Close-up view:
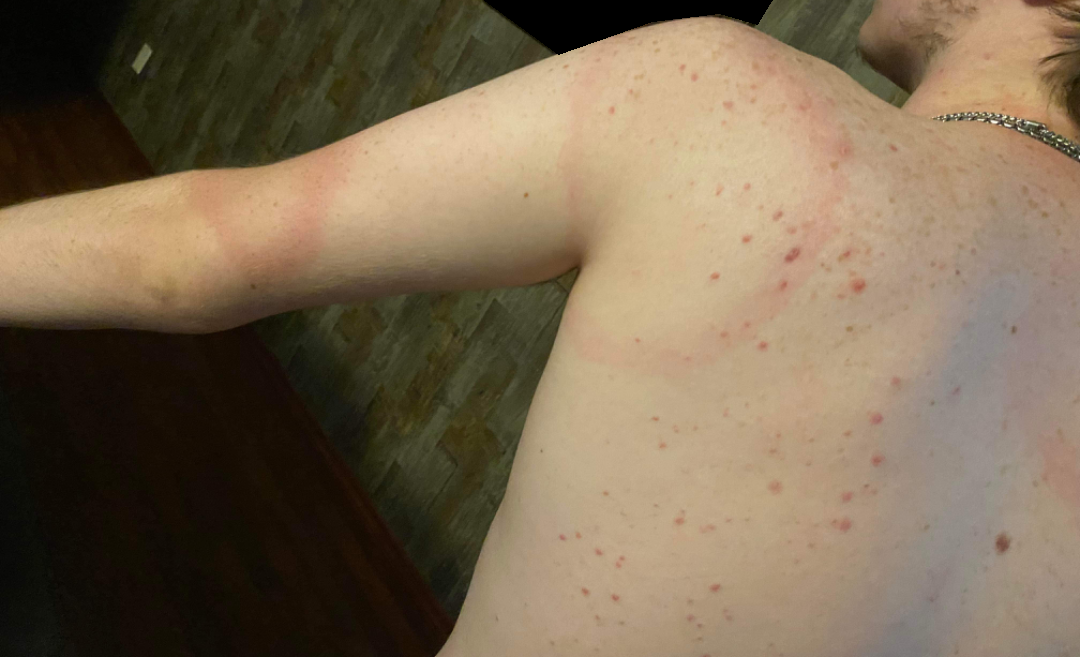Q: What was the assessment?
A: could not be assessed